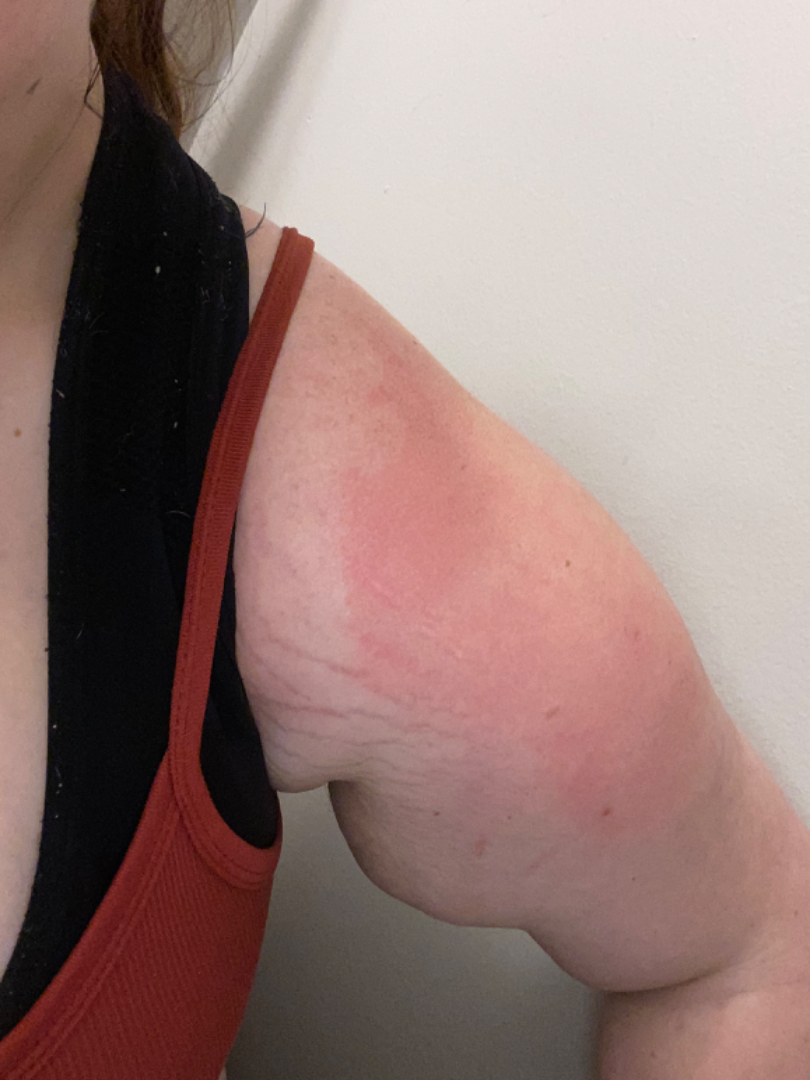Impression: The skin findings could not be characterized from the image. History: The arm and leg are involved. An image taken at a distance. The contributor is 18–29, female.